A clinical photo of a skin lesion taken with a smartphone. FST II. A female subject aged 84 — 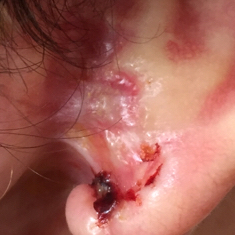Located on an ear. Per patient report, the lesion itches and has bled. Confirmed on histopathology as a lesion of indeterminate malignant potential — an actinic keratosis.